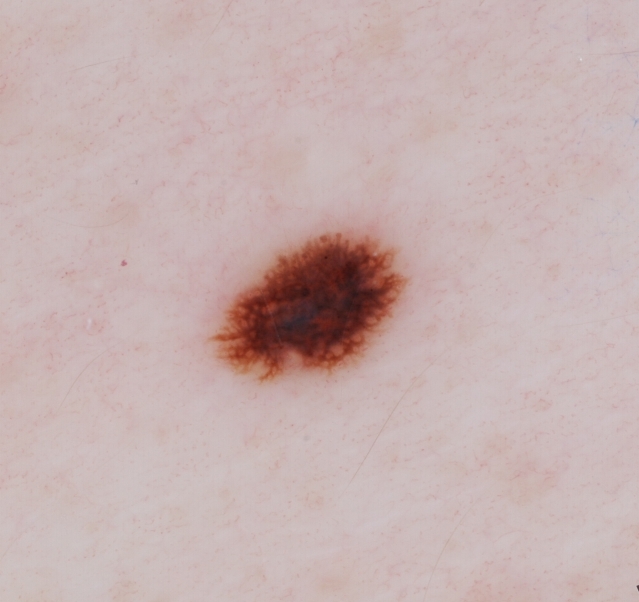A dermoscopy image of a single skin lesion. A male subject, aged 43 to 47. The lesion occupies the region [202, 215, 415, 386]. The lesion takes up about 6% of the image. On dermoscopy, the lesion shows streaks and pigment network. Biopsy-confirmed as a melanoma, a malignancy.